Texture is reported as rough or flaky; the photograph was taken at a distance; the lesion involves the head or neck; reported lesion symptoms include bleeding and itching:
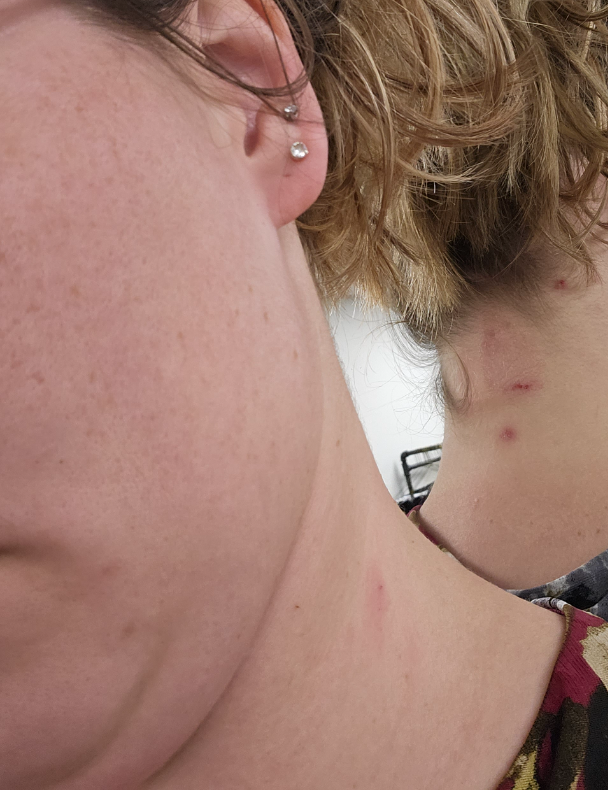differential — Psoriasis, Eczema and Lichen Simplex Chronicus were considered with similar weight.